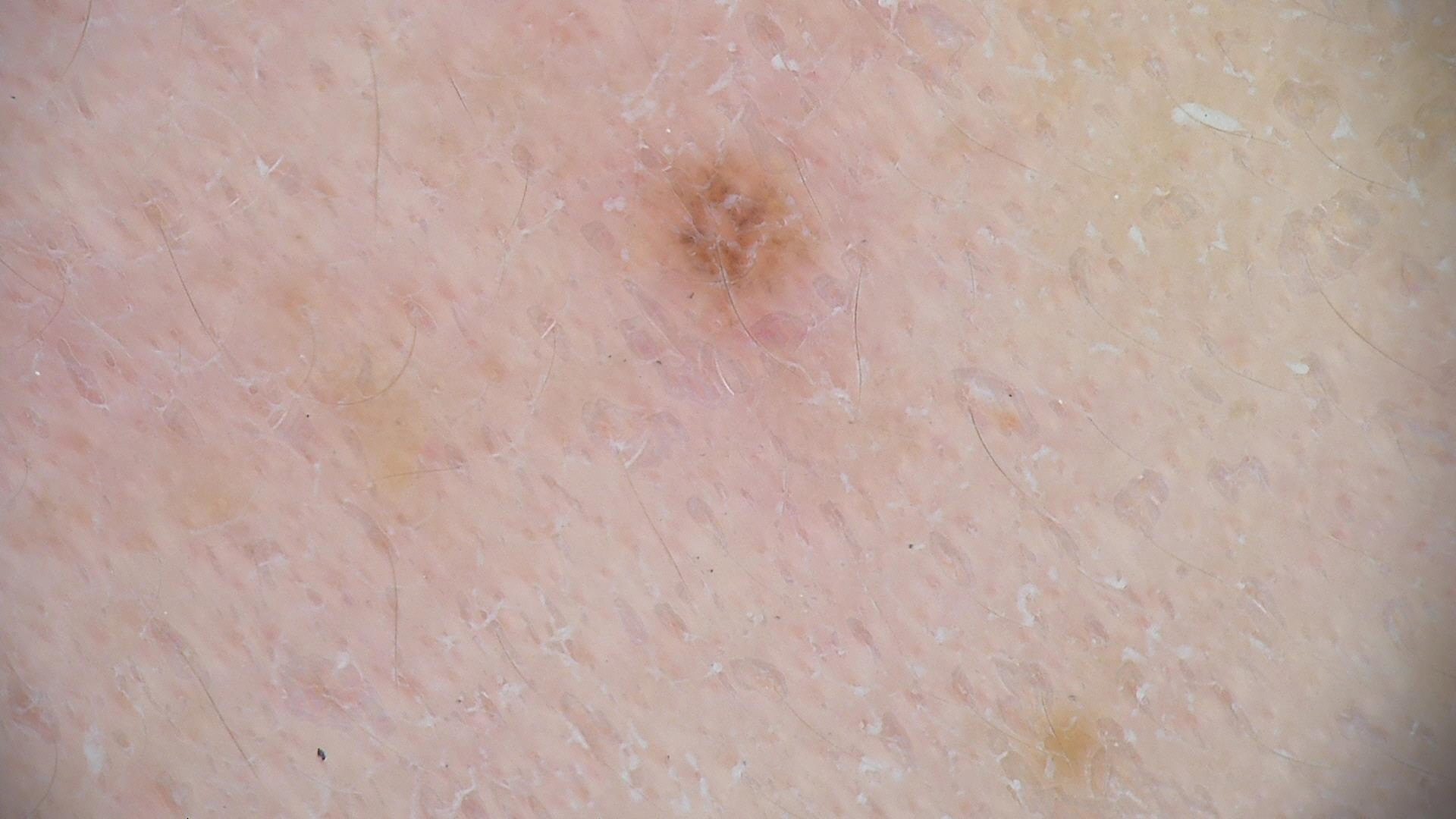A dermoscopic photograph of a skin lesion. The diagnosis was a dysplastic junctional nevus.